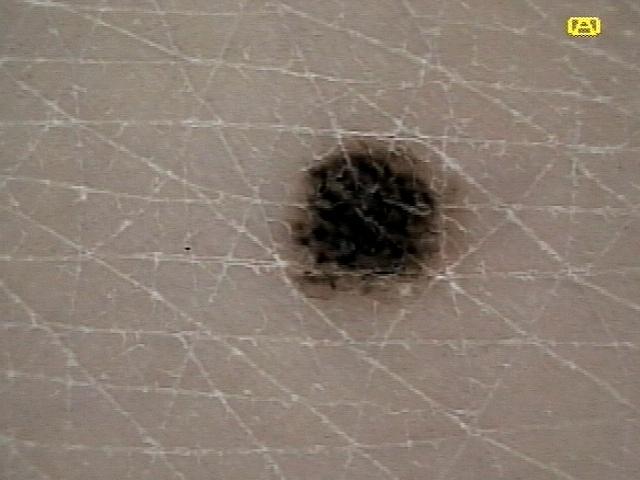{"patient": {"age_approx": 35, "sex": "female"}, "image": "dermoscopic image", "melanoma_history": {"personal_hx_melanoma": true}, "lesion_location": {"region": "a lower extremity"}, "diagnosis": {"name": "Nevus", "malignancy": "benign", "confirmation": "histopathology", "lineage": "melanocytic"}}